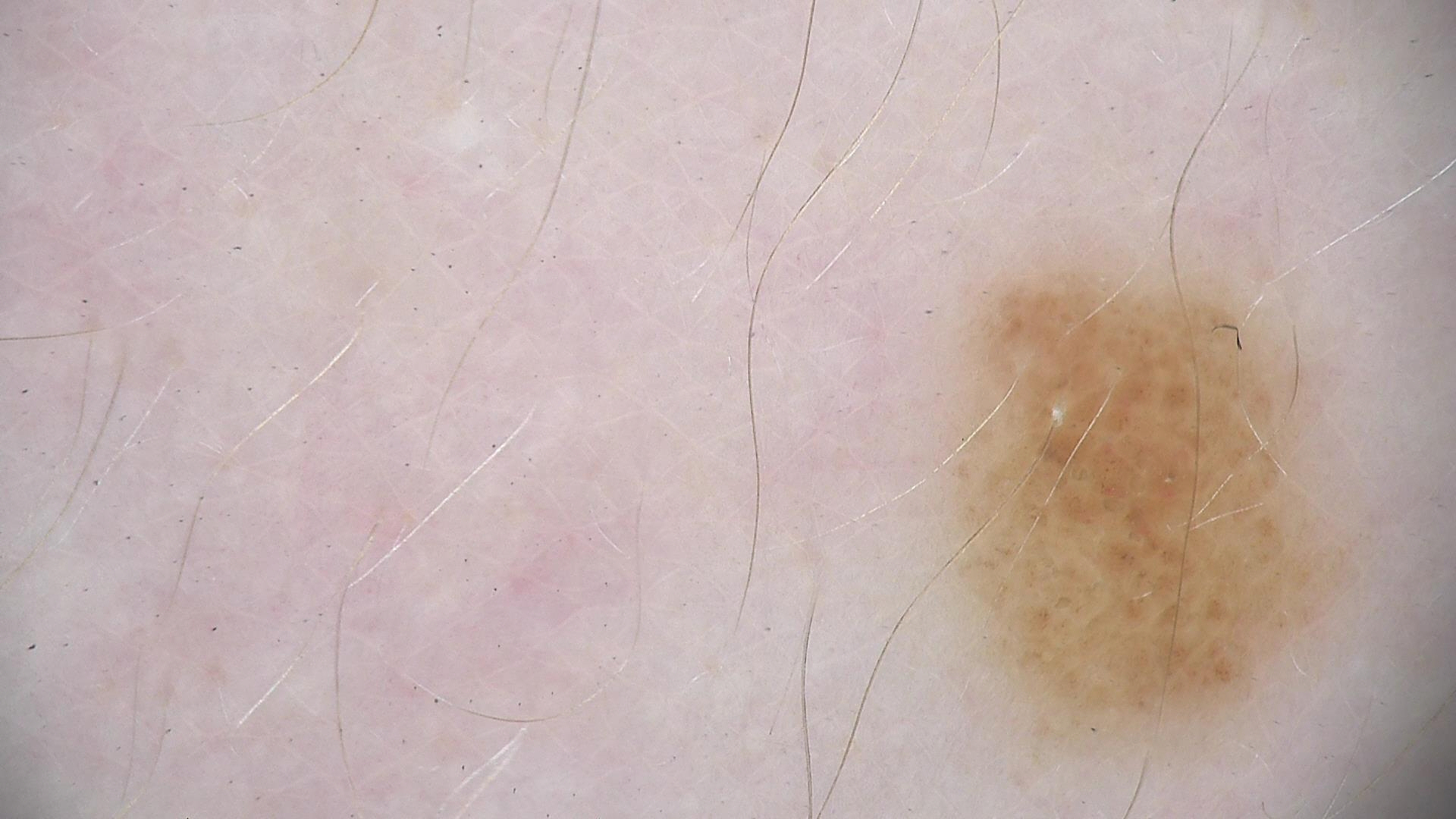imaging = dermatoscopy
assessment = junctional nevus (expert consensus)